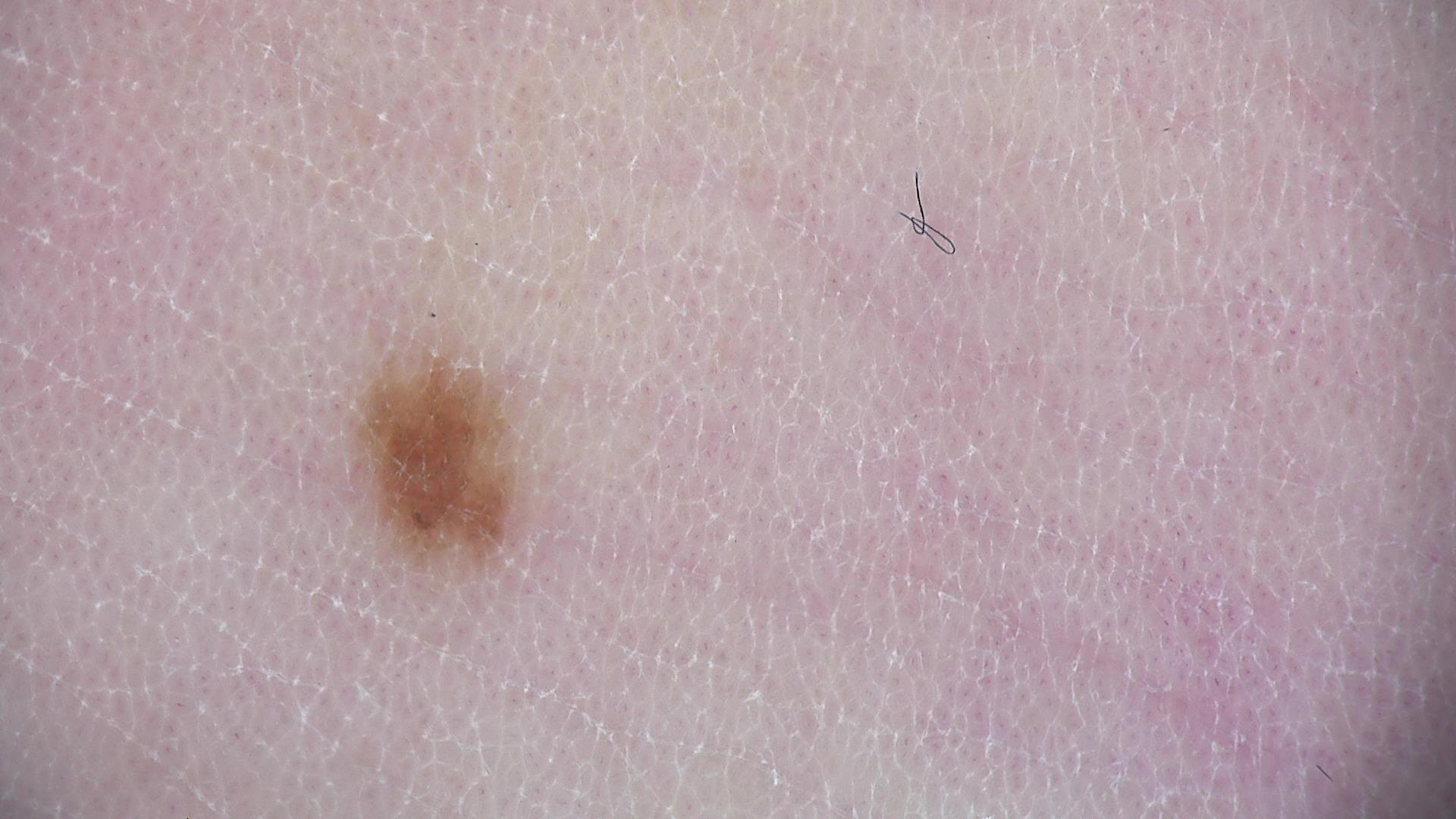Impression:
Consistent with an acral junctional nevus.